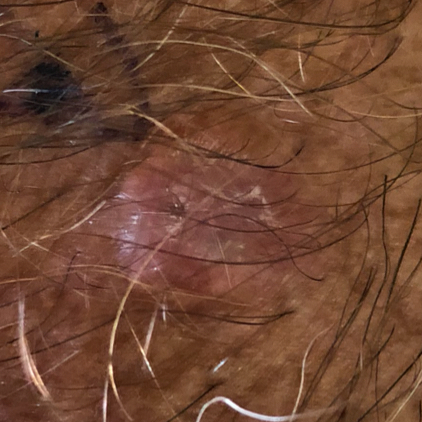Q: What is the imaging modality?
A: smartphone clinical photo
Q: Who is the patient?
A: male, age 78
Q: Where on the body is the lesion?
A: a forearm
Q: What is the diagnosis?
A: basal cell carcinoma (biopsy-proven)